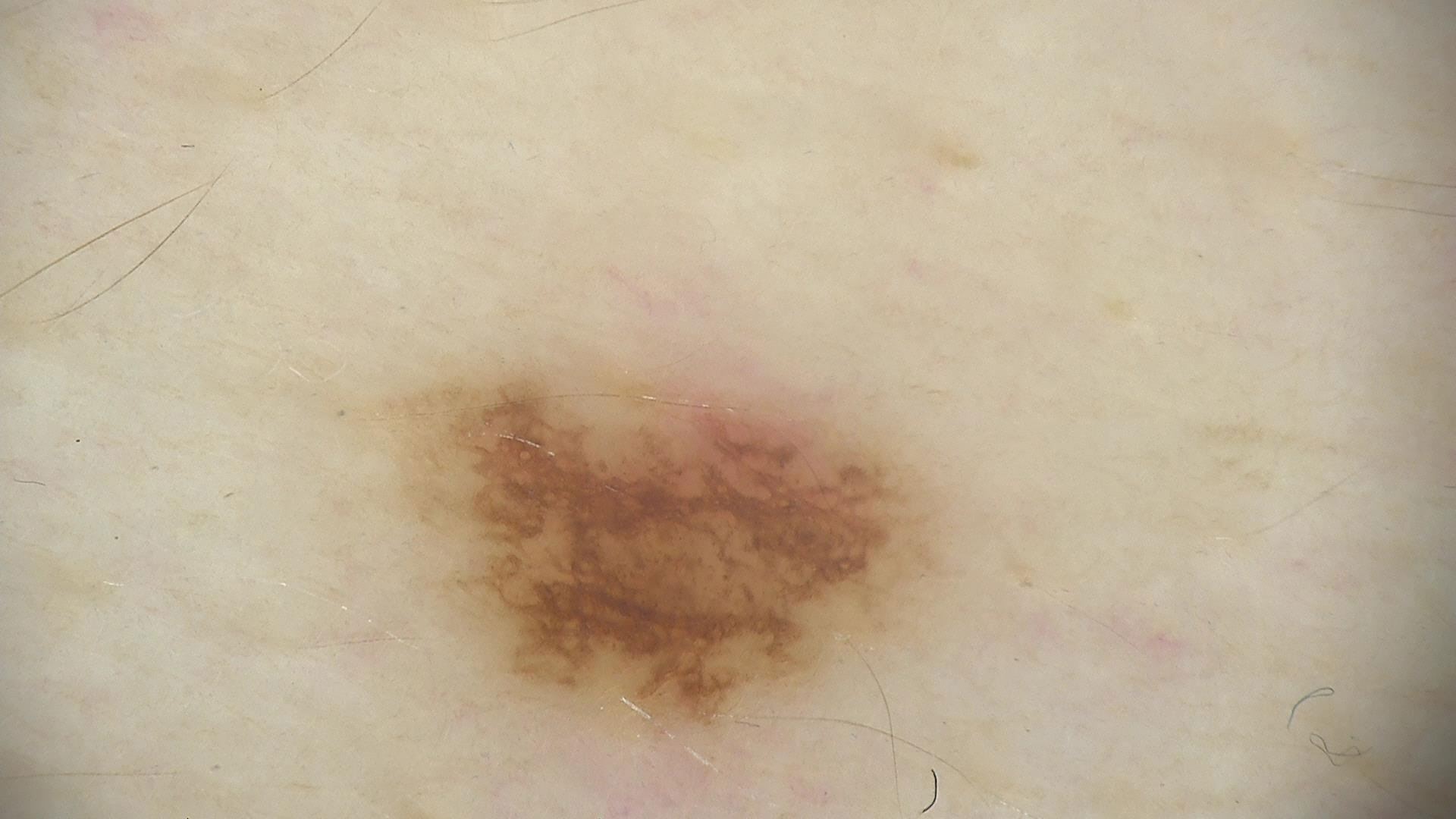image type: dermatoscopy; label: dysplastic junctional nevus (expert consensus).